A dermoscopic close-up of a skin lesion.
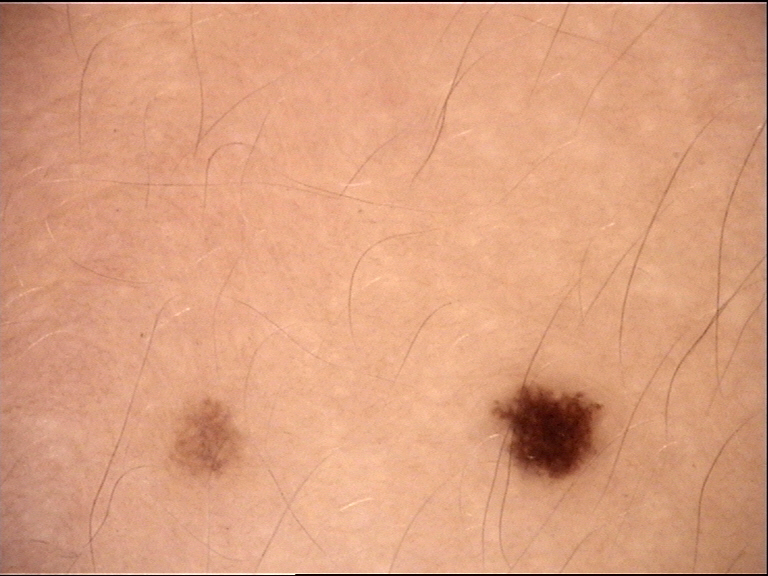Consistent with a benign lesion — a dysplastic junctional nevus.